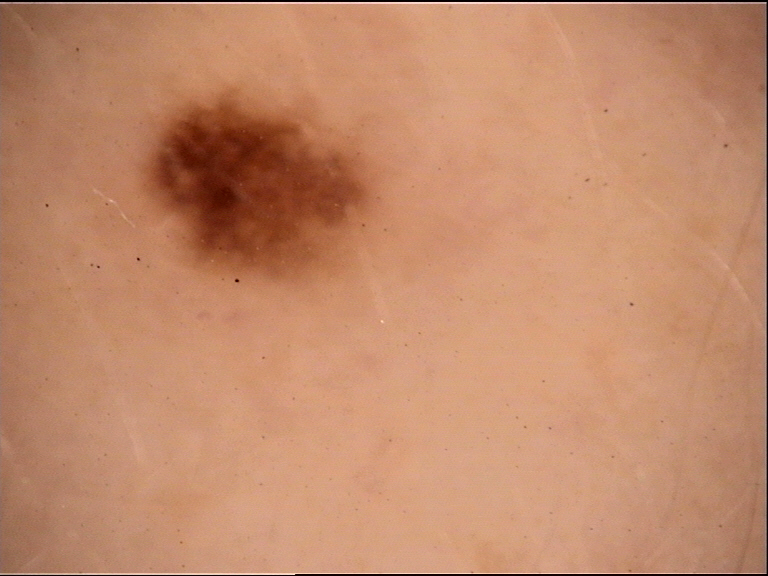A dermoscopic image of a skin lesion. Consistent with a dysplastic junctional nevus.